The lesion is associated with itching; the arm is involved; self-categorized by the patient as skin that appeared healthy to them; the condition has been present for one to four weeks; the contributor is 50–59, male; this is a close-up image; the contributor notes the lesion is rough or flaky and raised or bumpy — 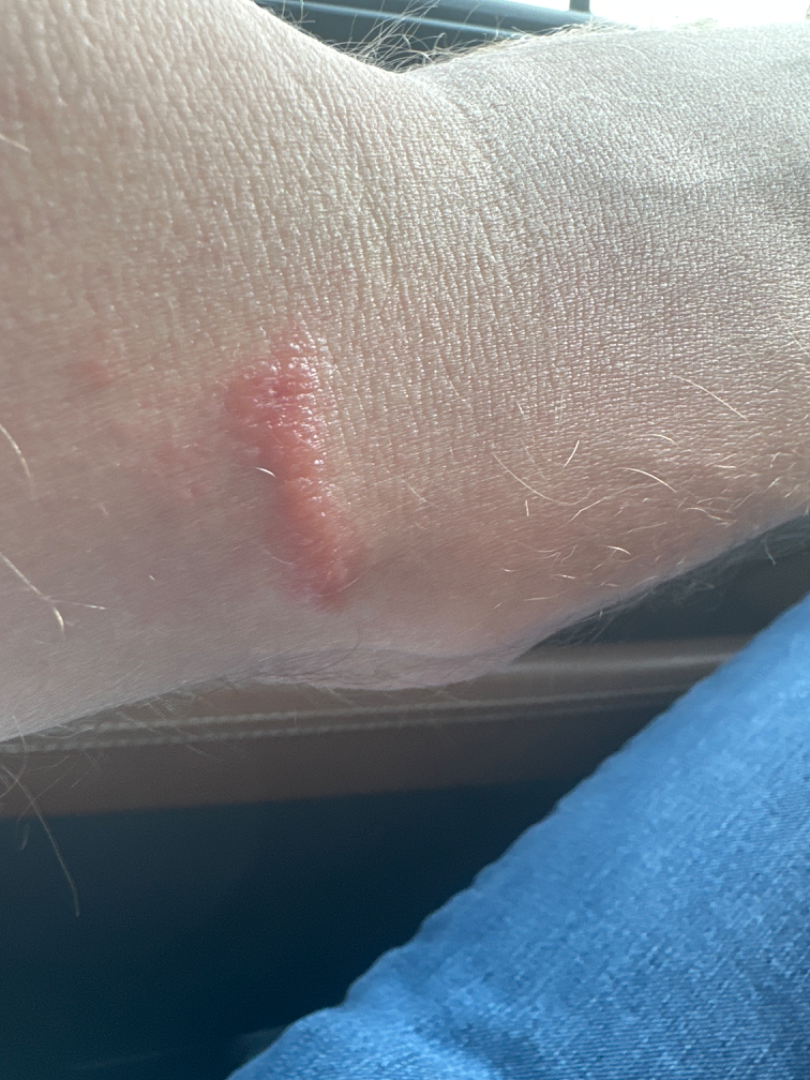On remote review of the image: the favored diagnosis is Allergic Contact Dermatitis; the differential also includes Insect Bite.